This is a close-up image · the subject is 18–29, male · the lesion involves the arm.
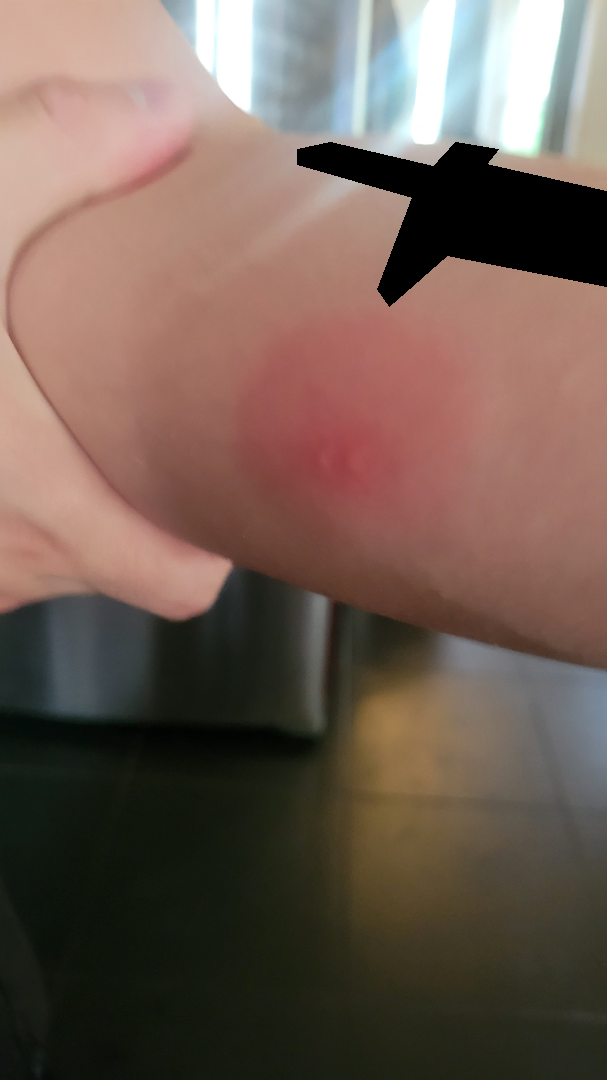Impression:
On remote dermatologist review, most consistent with Insect Bite; the differential also includes Erythema migrans.